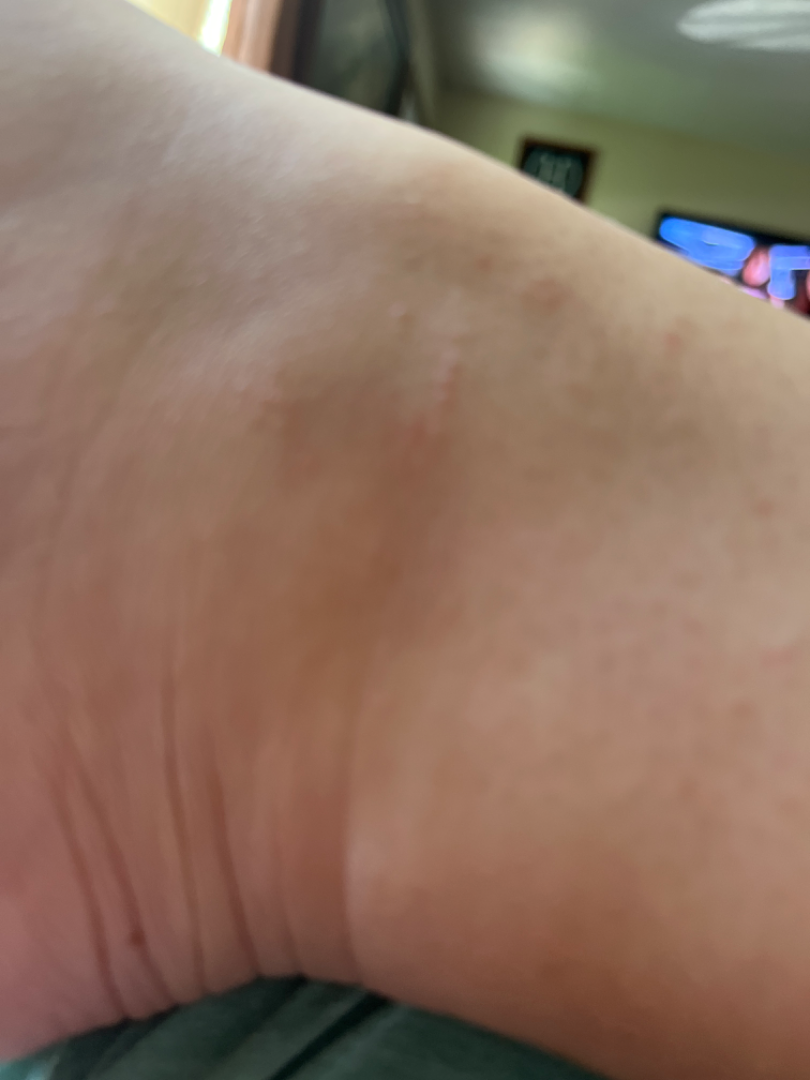The reviewing dermatologist was unable to assign a differential diagnosis from the image.
The photograph is a close-up of the affected area.
The lesion is described as raised or bumpy.
The patient reports itching.
The lesion involves the leg.
The patient is 40–49, female.
The condition has been present for one to four weeks.
Self-categorized by the patient as a rash.